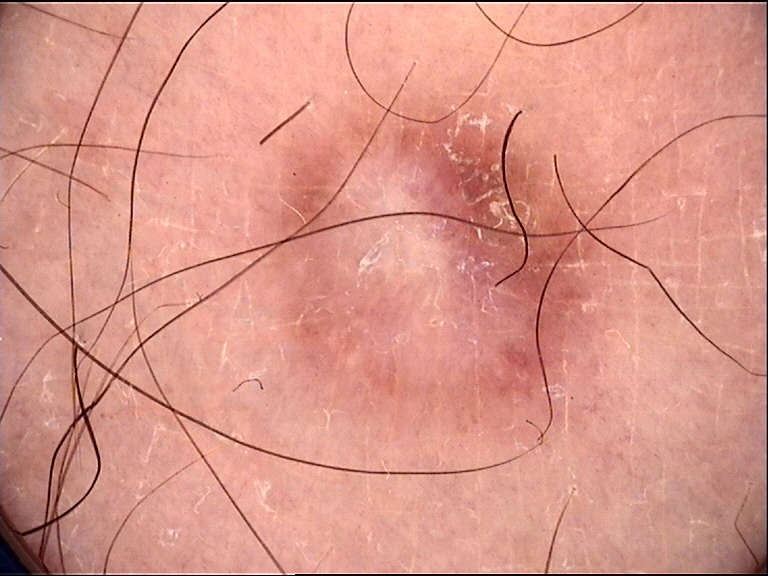The diagnostic label was a fibro-histiocytic, benign lesion — a dermatofibroma.